A dermoscopy image of a single skin lesion: 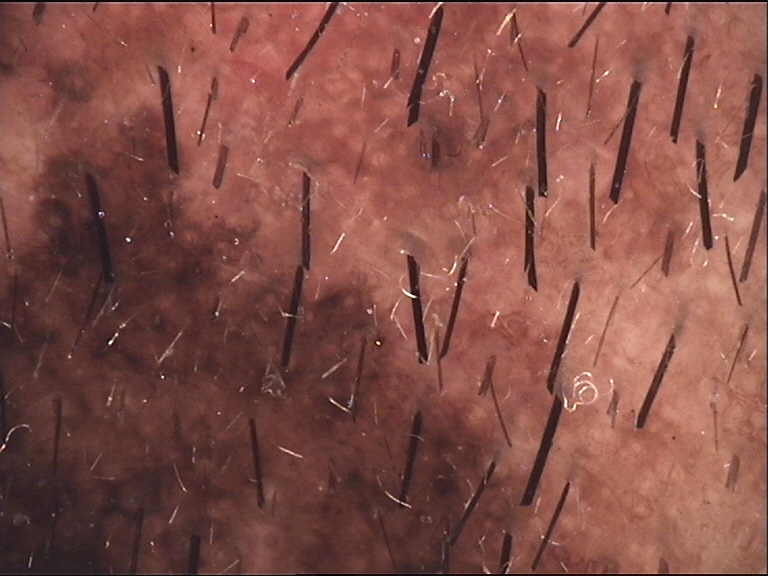The architecture is that of a banal lesion.
The diagnostic label was a congenital compound nevus.